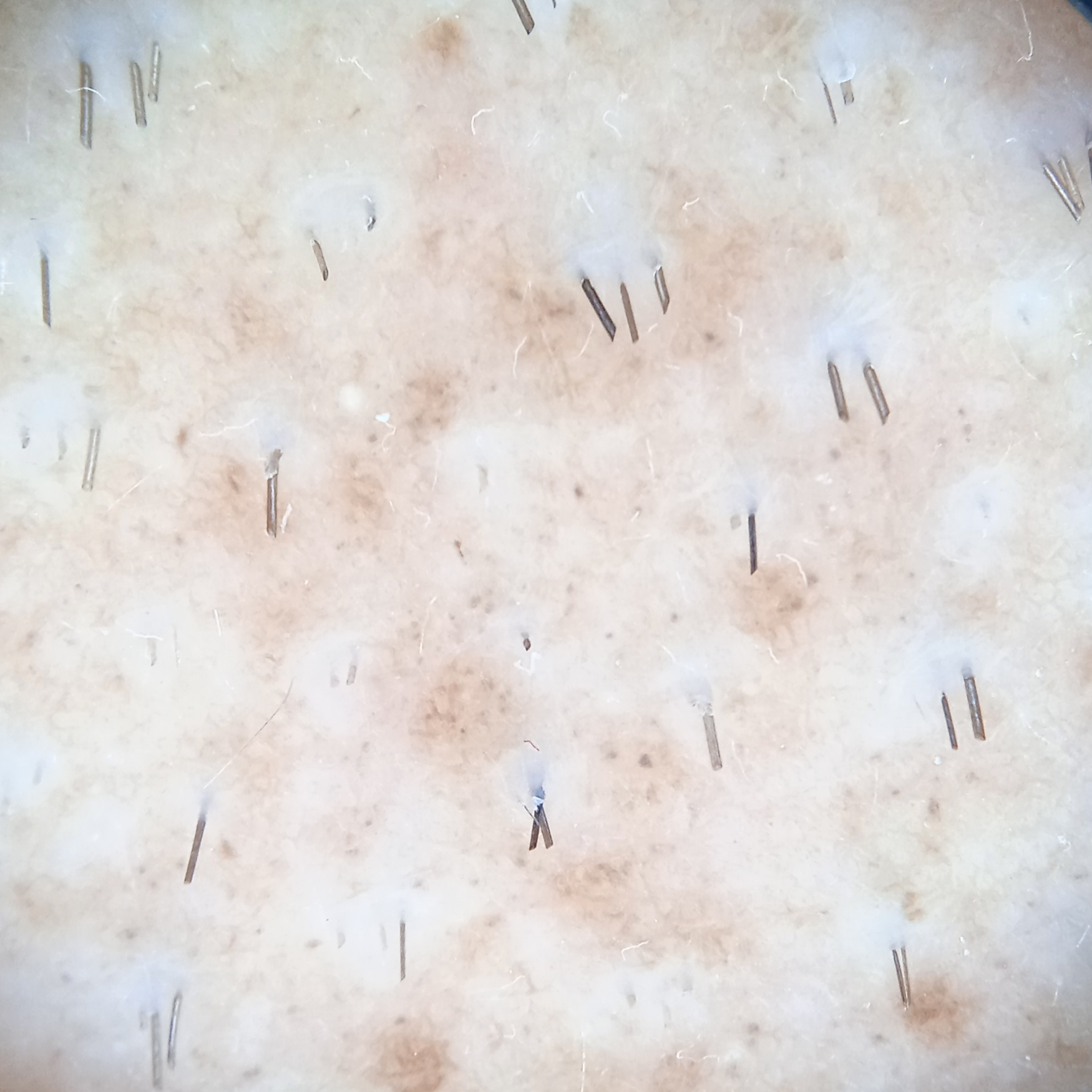A male patient 15 years of age.
The patient describes having few moles overall.
The patient says their skin tans without first burning.
Referred with a clinical suspicion of melanocytic nevus.
A dermoscopy image of a skin lesion.
The lesion involves an arm.
Measuring roughly 26.1 mm.
Histopathologically confirmed as a melanocytic nevus, following a punch biopsy.